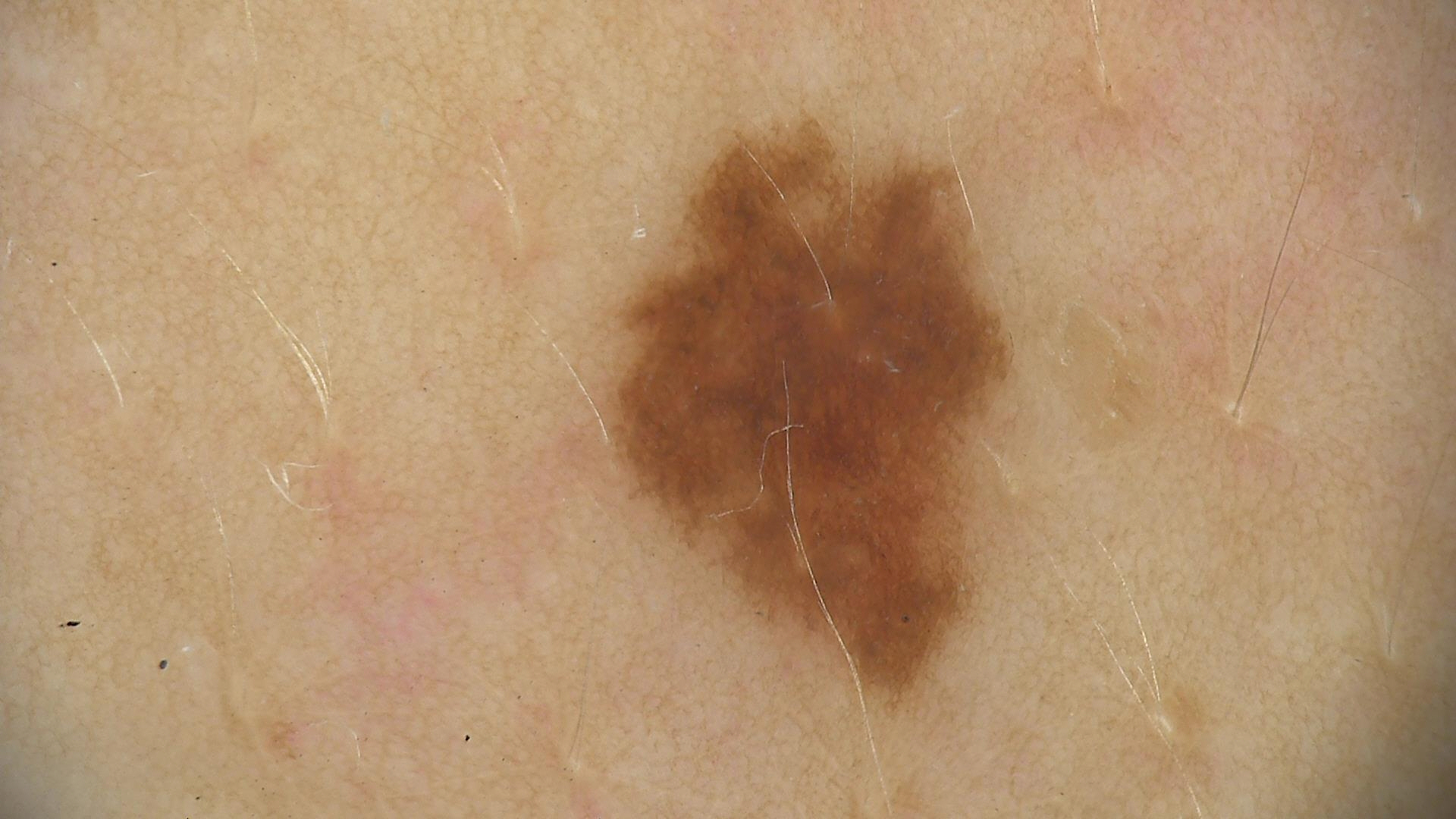A dermoscopic photograph of a skin lesion. Labeled as a dysplastic junctional nevus.